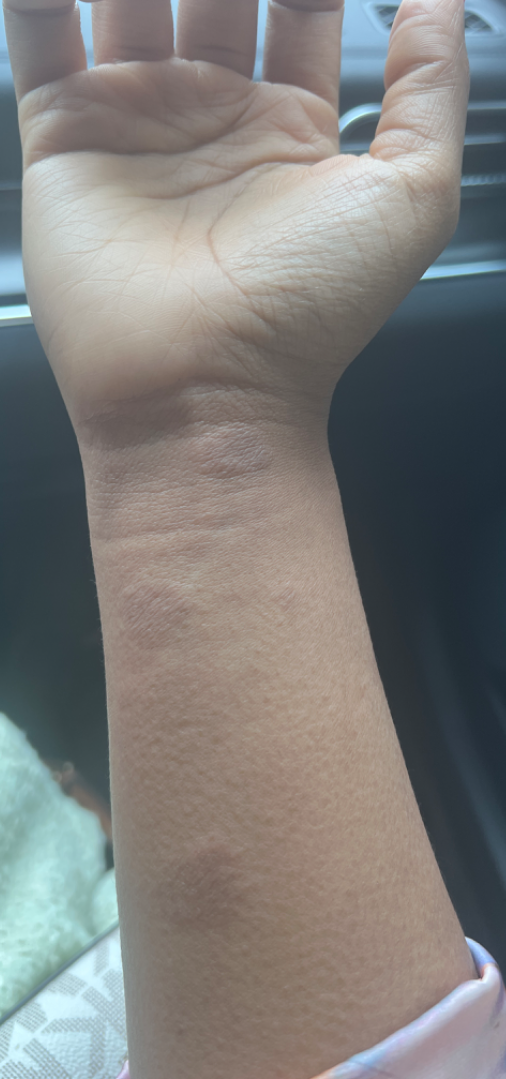Q: What is the dermatologist's impression?
A: Eczema (favored)